The chart documents no previous melanoma and no melanoma in first-degree relatives. A contact-polarized dermoscopy image of a skin lesion. A male subject aged 38 to 42 — 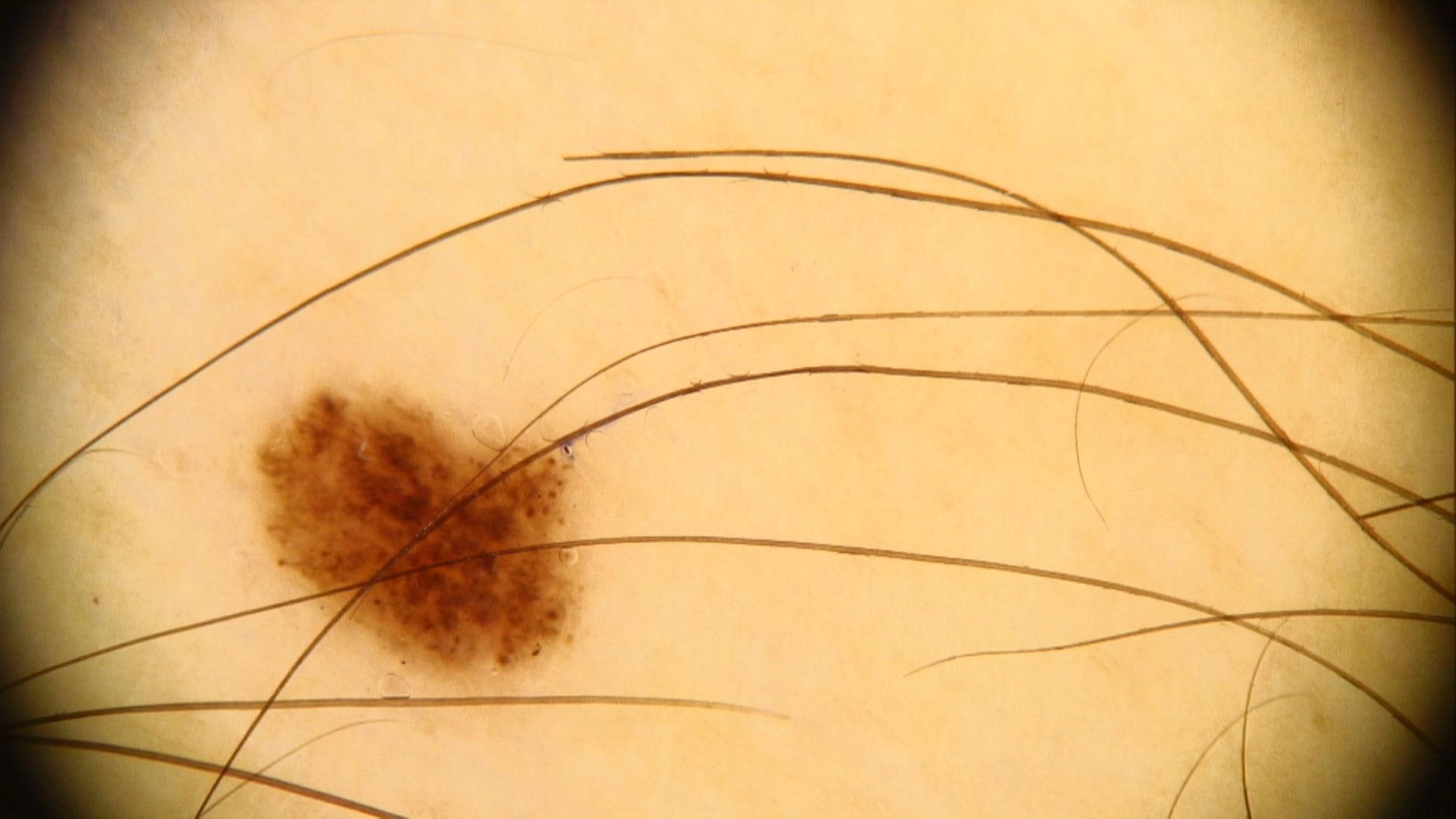Notes:
* impression · Nevus